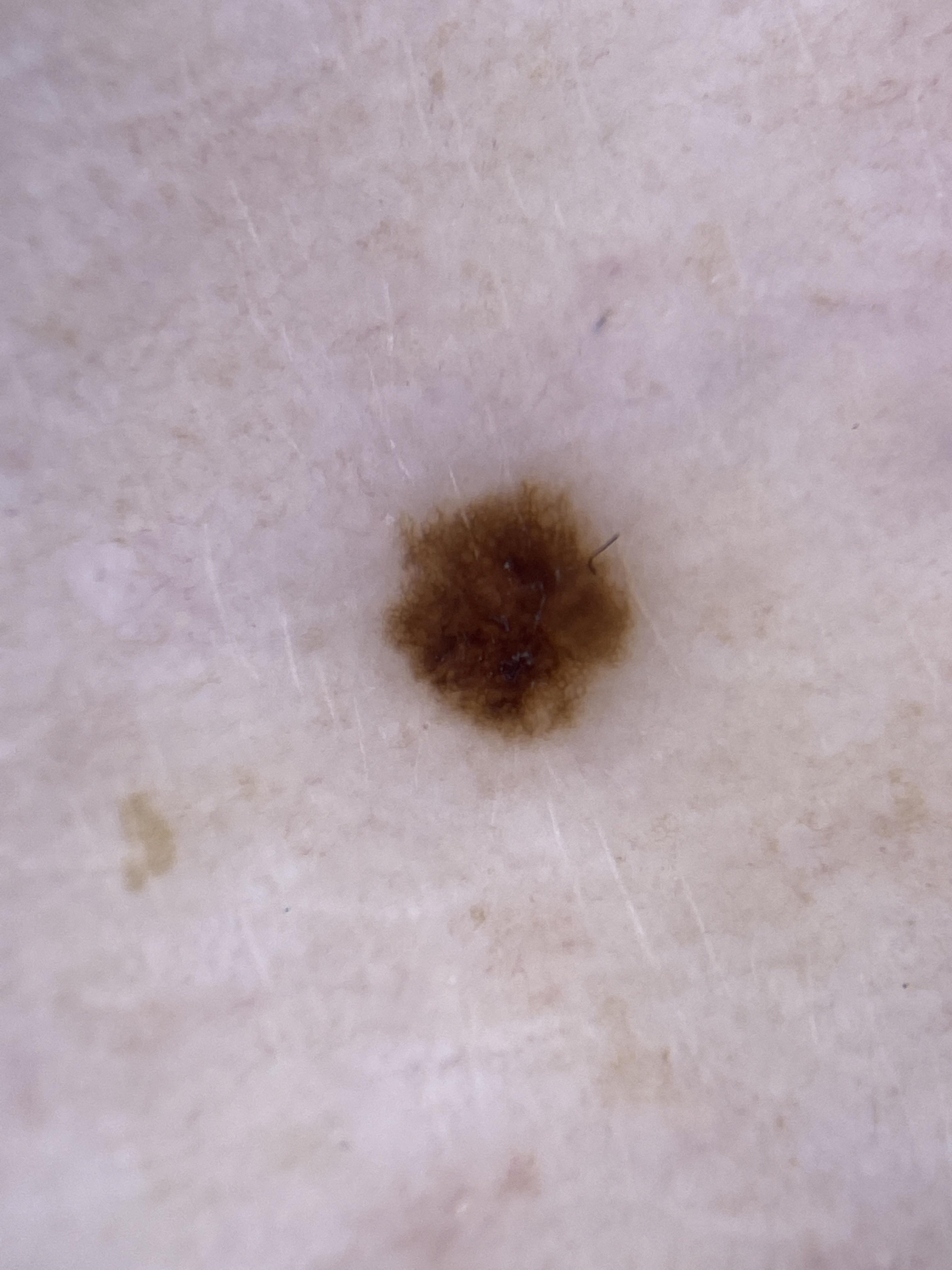* patient · female, about 55 years old
* modality · dermoscopic image
* anatomic site · the trunk
* diagnostic label · Nevus (clinical impression)